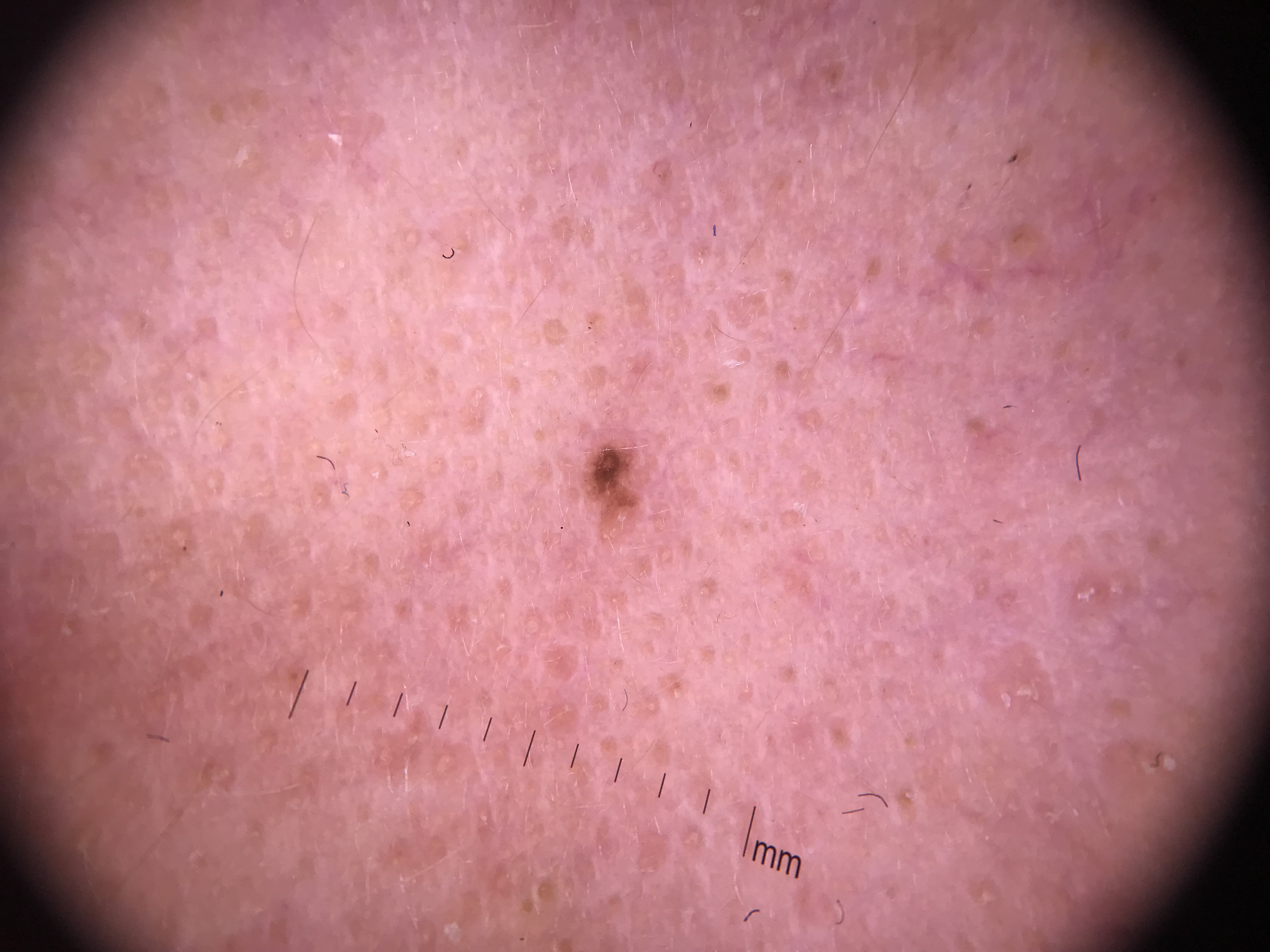Q: What was the diagnostic impression?
A: junctional nevus (expert consensus)